A skin lesion imaged with a dermatoscope: 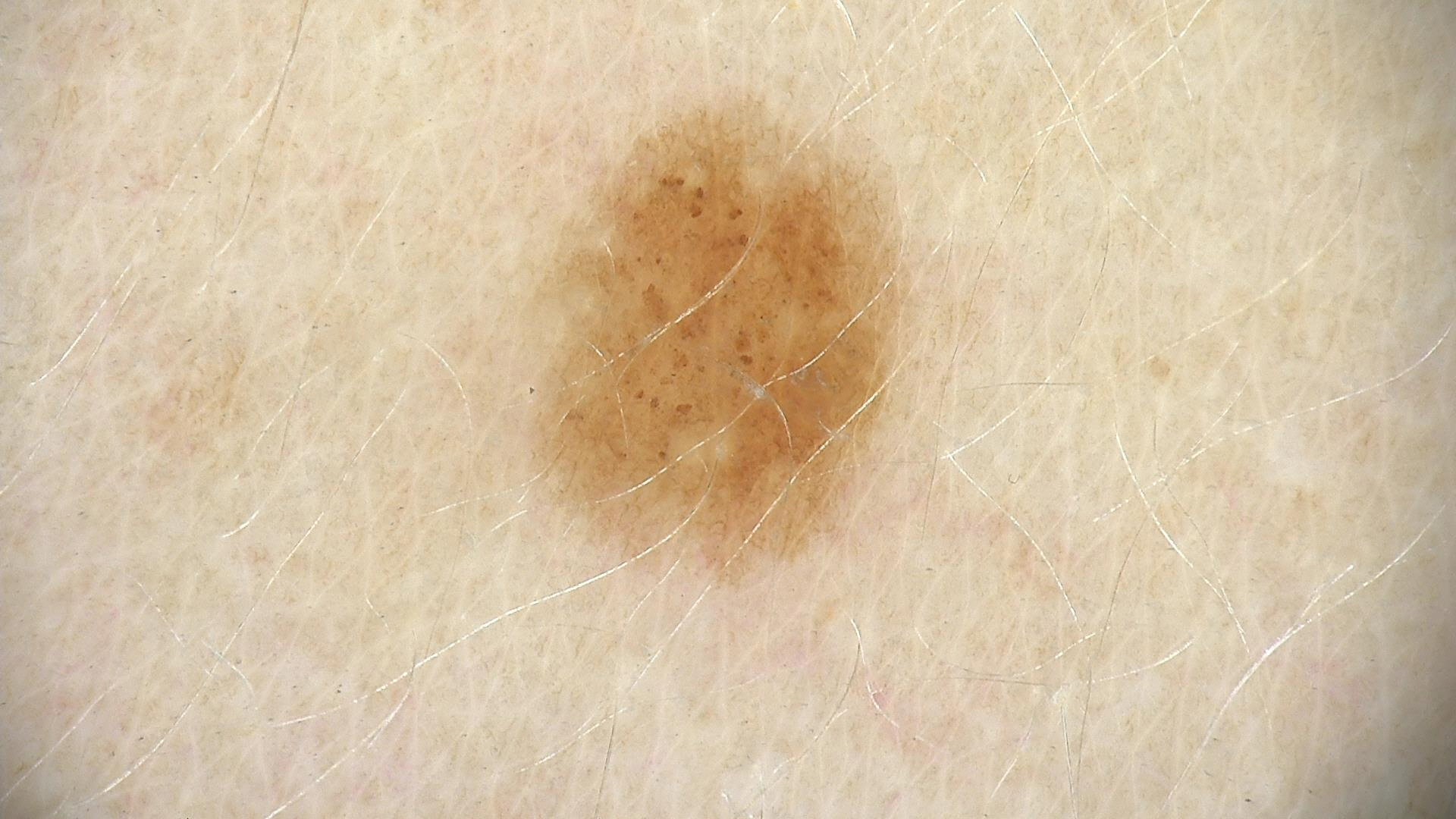The diagnostic label was a dysplastic junctional nevus.